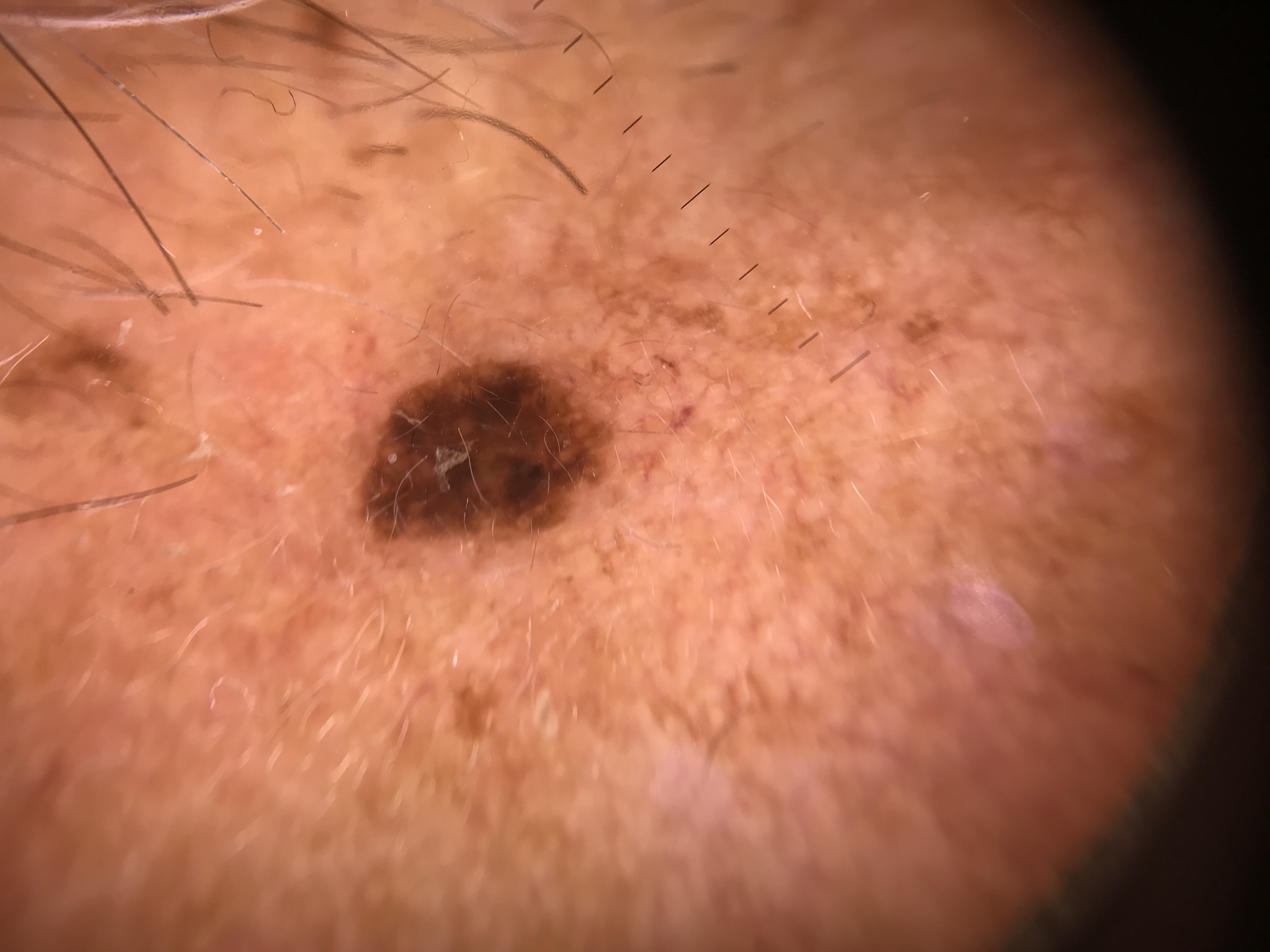The diagnosis was a seborrheic keratosis.